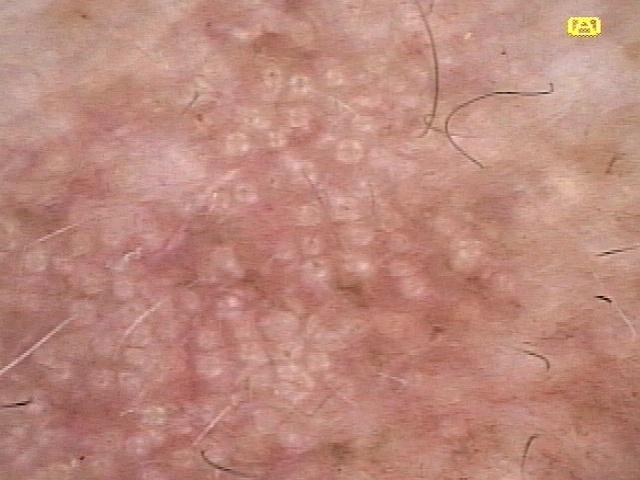Summary: A male patient roughly 70 years of age. Impression: Clinically diagnosed as a solar or actinic keratosis.